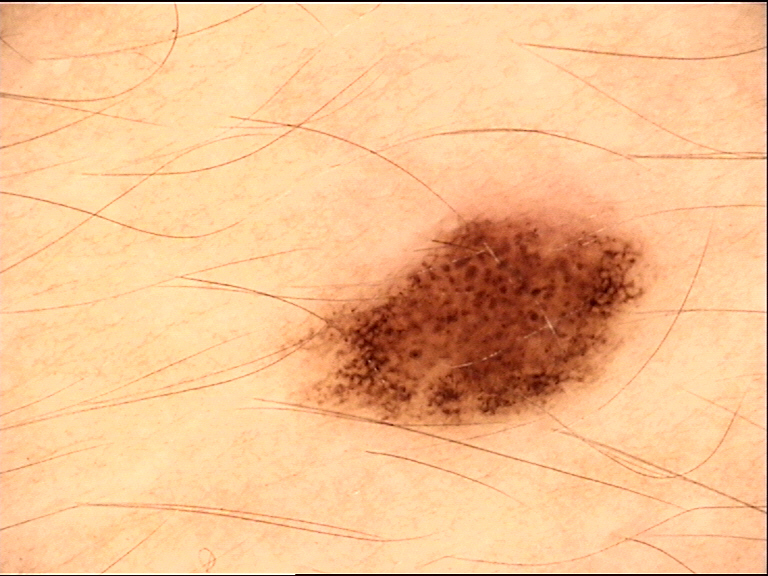Dermoscopy of a skin lesion.
The morphology is that of a banal lesion.
The diagnostic label was a compound nevus.